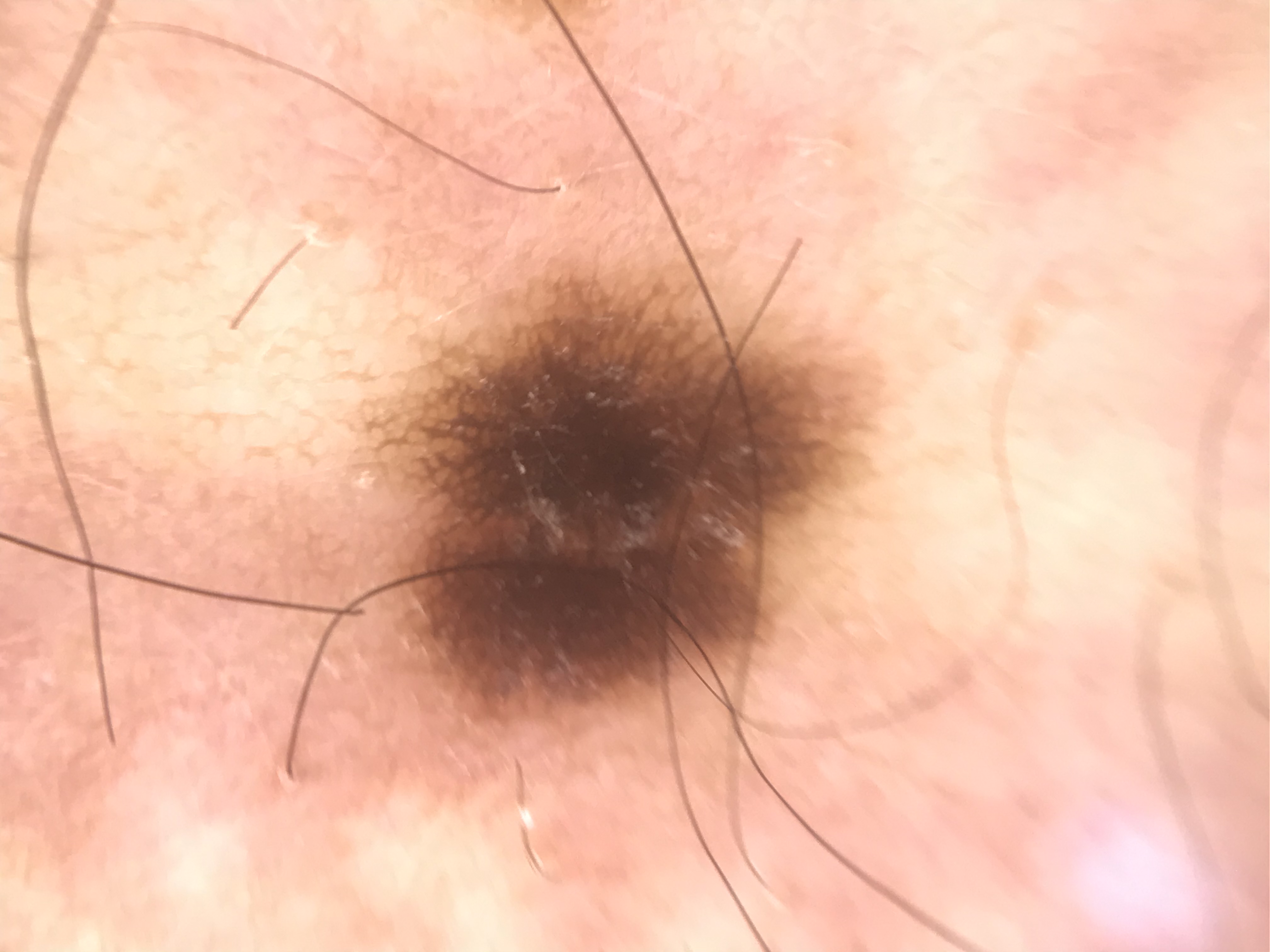Q: What kind of image is this?
A: dermatoscopy
Q: What was the diagnostic impression?
A: junctional nevus (expert consensus)